This is a close-up image, located on the arm, the contributor is a female aged 50–59: 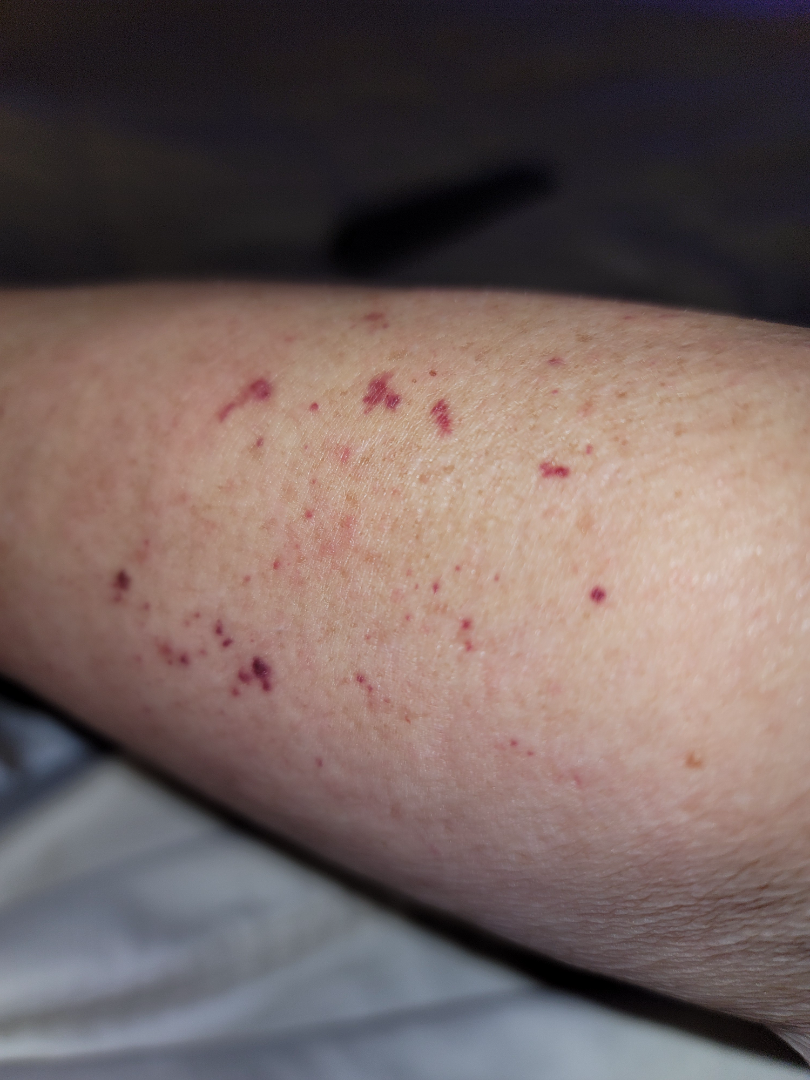Findings:
• texture: flat
• skin tone: Fitzpatrick phototype II
• reported symptoms: bothersome appearance and enlargement
• self-categorized as: a pigmentary problem
• onset: less than one week
• diagnostic considerations: most consistent with Eczema